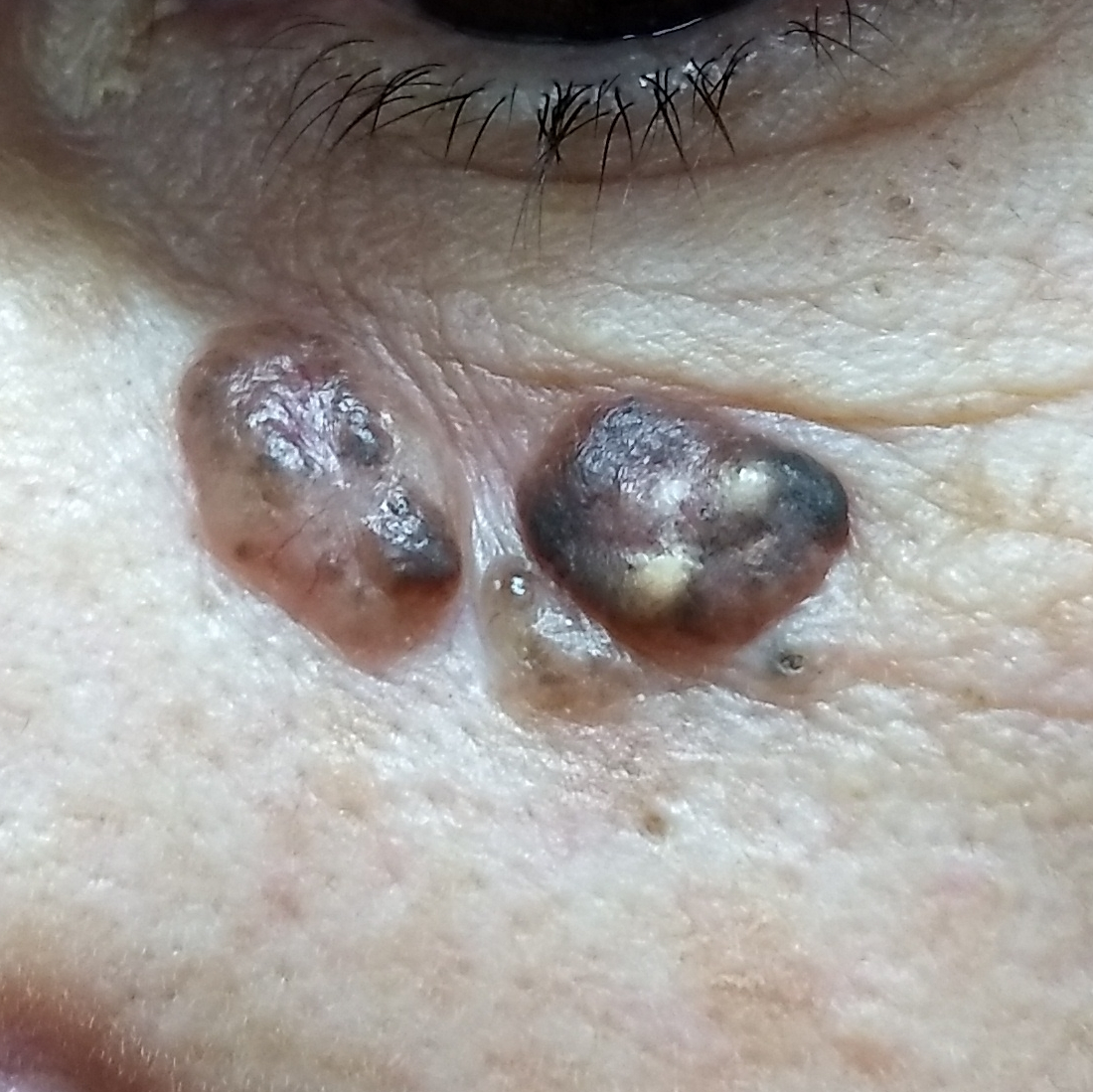Clinical context: A female subject 60 years old. By history, pesticide exposure, no prior malignancy (patient or family), and no prior skin cancer (patient or family). The lesion is on the face. The patient reports that the lesion has grown and is elevated. Diagnosis: Histopathological examination showed a basal cell carcinoma.